The lesion is described as rough or flaky and raised or bumpy · no constitutional symptoms were reported · the patient is a female aged 18–29 · the photograph is a close-up of the affected area · the condition has been present for one to four weeks · Fitzpatrick phototype II; lay reviewers estimated Monk skin tone scale 1 · located on the arm · the patient reports itching:
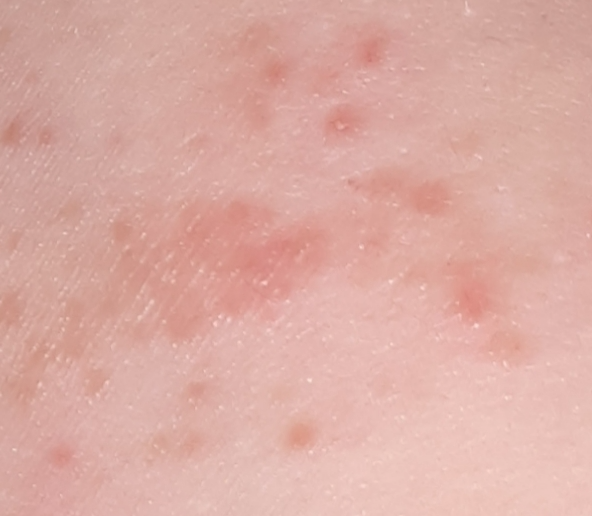Findings:
The reviewer was unable to grade this case for skin condition.